The lesion involves the back of the torso and front of the torso. The patient notes the condition has been present for less than one week. The photograph is a close-up of the affected area. The patient notes bothersome appearance and itching. Male patient, age 40–49. No associated systemic symptoms reported. The patient considered this a rash.
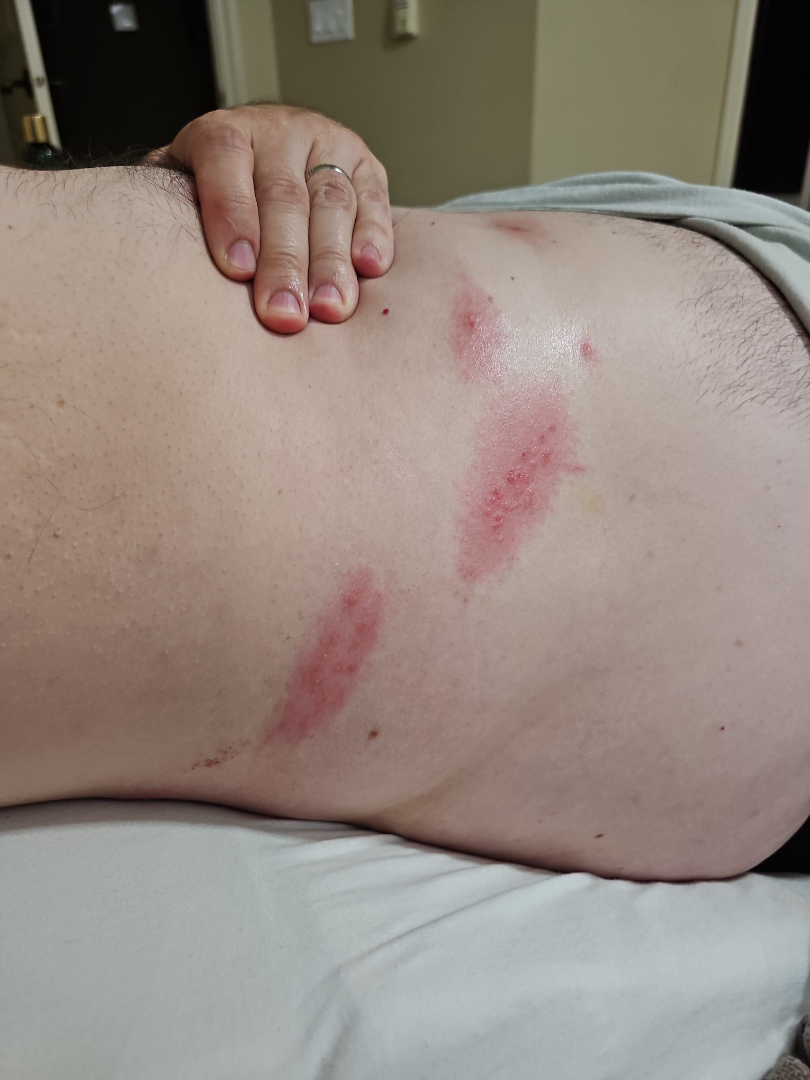– assessment · indeterminate from the photograph